A dermoscopic image of a skin lesion · few moles overall by the patient's own estimate · a male subject aged 66 · the patient says their skin reddens with sun exposure: 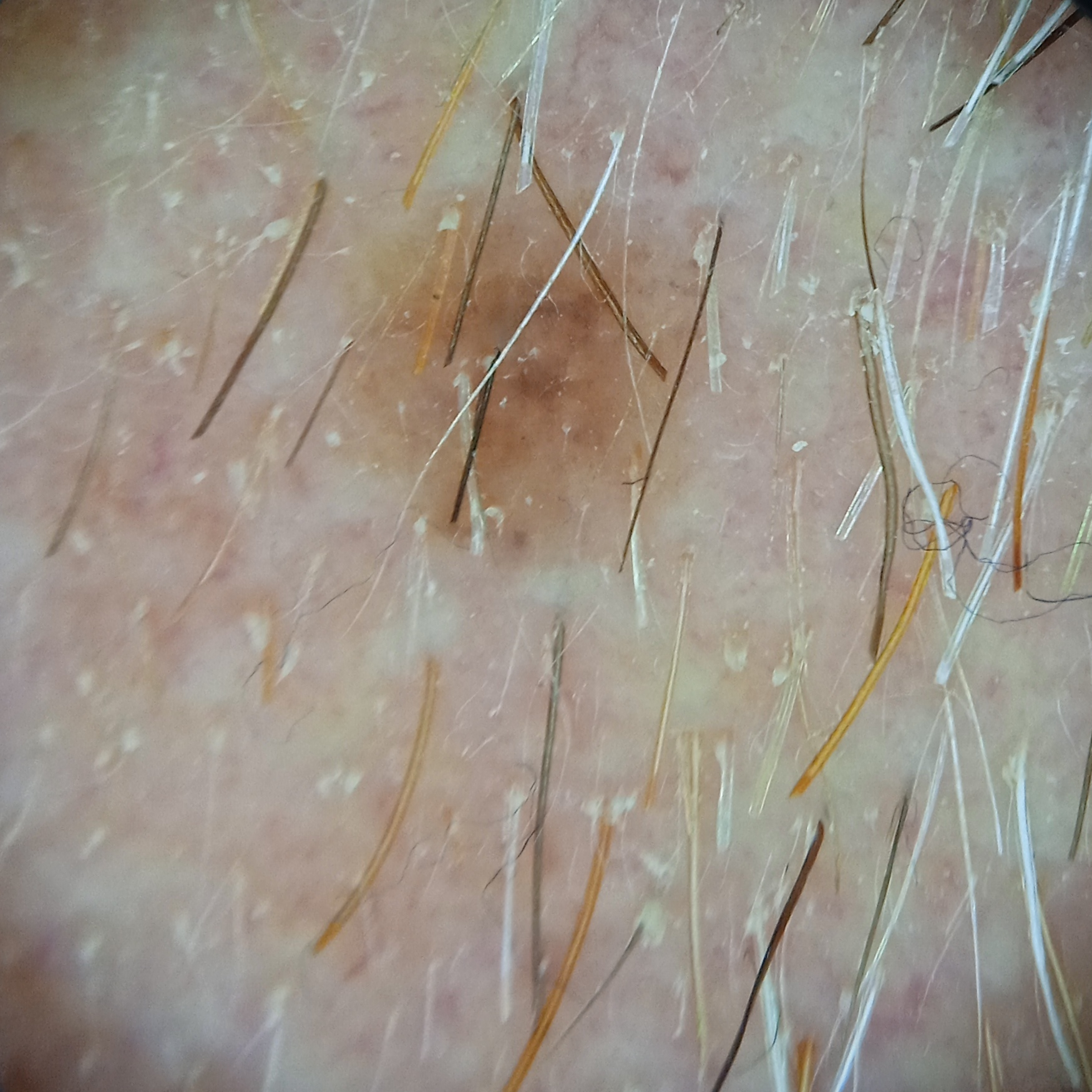Clinical context:
The lesion involves the face. The lesion measures approximately 3.7 mm.
Assessment:
The diagnostic impression was a melanocytic nevus.